The photo was captured at a distance: 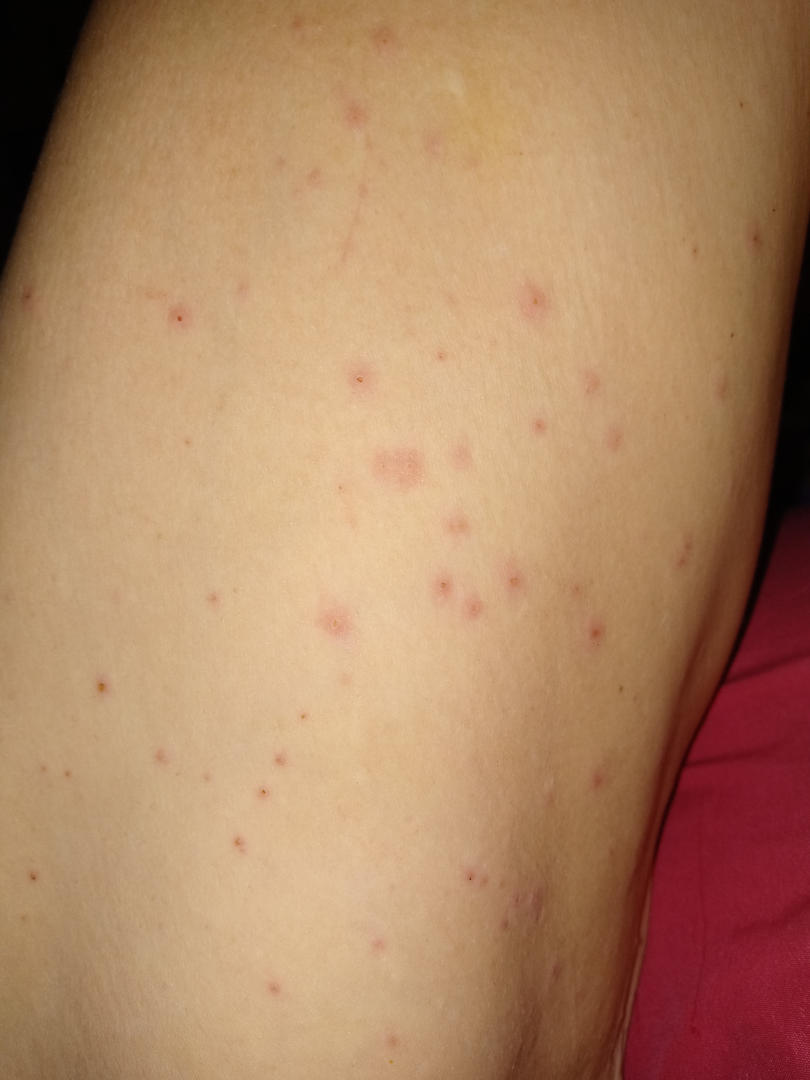clinical impression = favoring Hypersensitivity.